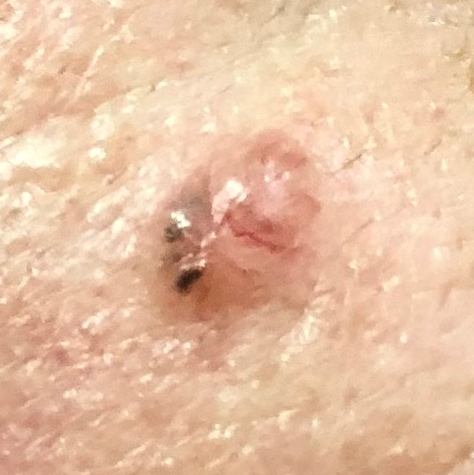A male subject aged 55. A clinical photograph of a skin lesion. Located on the face. The lesion is roughly 5 by 4 mm. Histopathology confirmed a basal cell carcinoma.